A female subject, aged around 25; dermoscopy of a skin lesion: 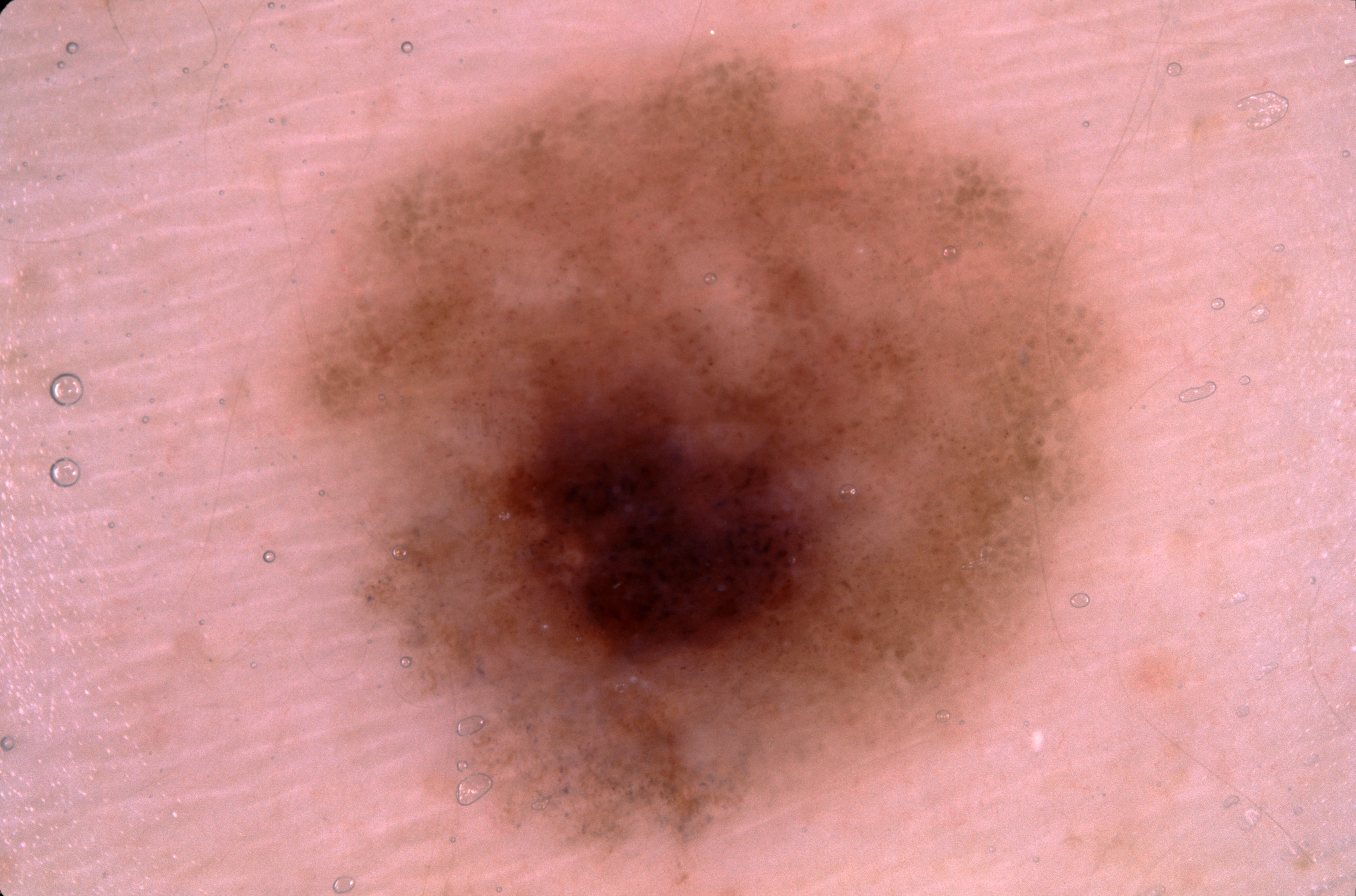Q: What does dermoscopy show?
A: negative network; absent: pigment network, streaks, and milia-like cysts
Q: Where is the lesion in the image?
A: <bbox>277, 37, 1122, 886</bbox>
Q: How much of the field does the lesion occupy?
A: ~40% of the field
Q: What is the diagnosis?
A: a melanocytic nevus, a benign lesion